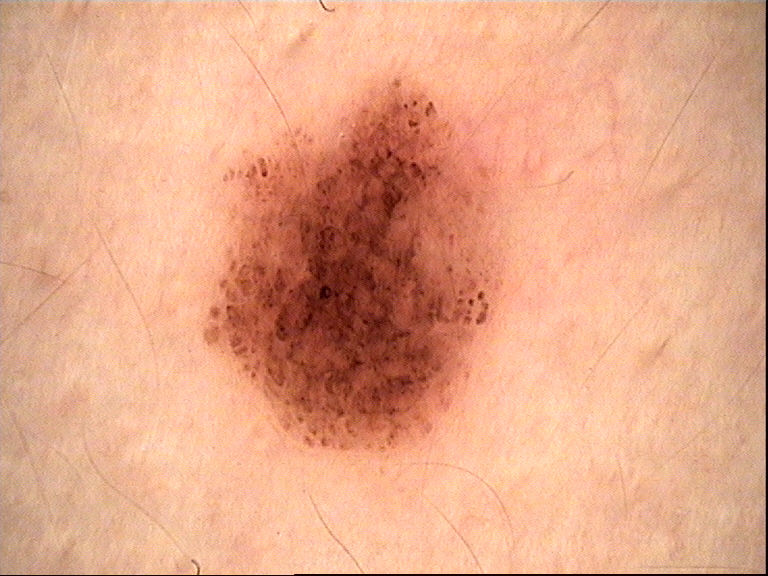A dermoscopic image of a skin lesion.
Labeled as a benign lesion — a dysplastic compound nevus.